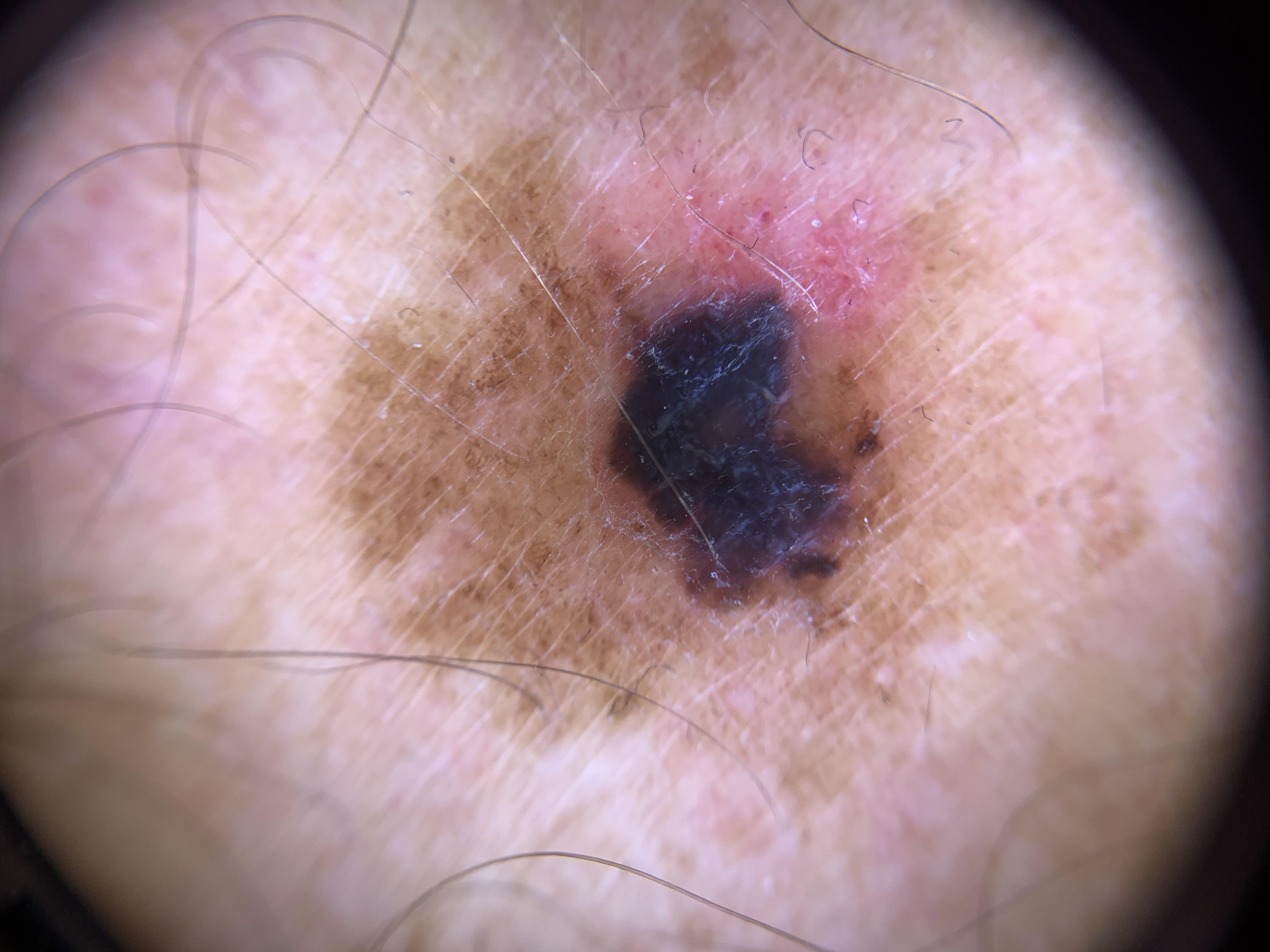| field | value |
|---|---|
| subject | male, aged 58-62 |
| site | a lower extremity |
| diagnostic label | Melanoma (biopsy-proven) |